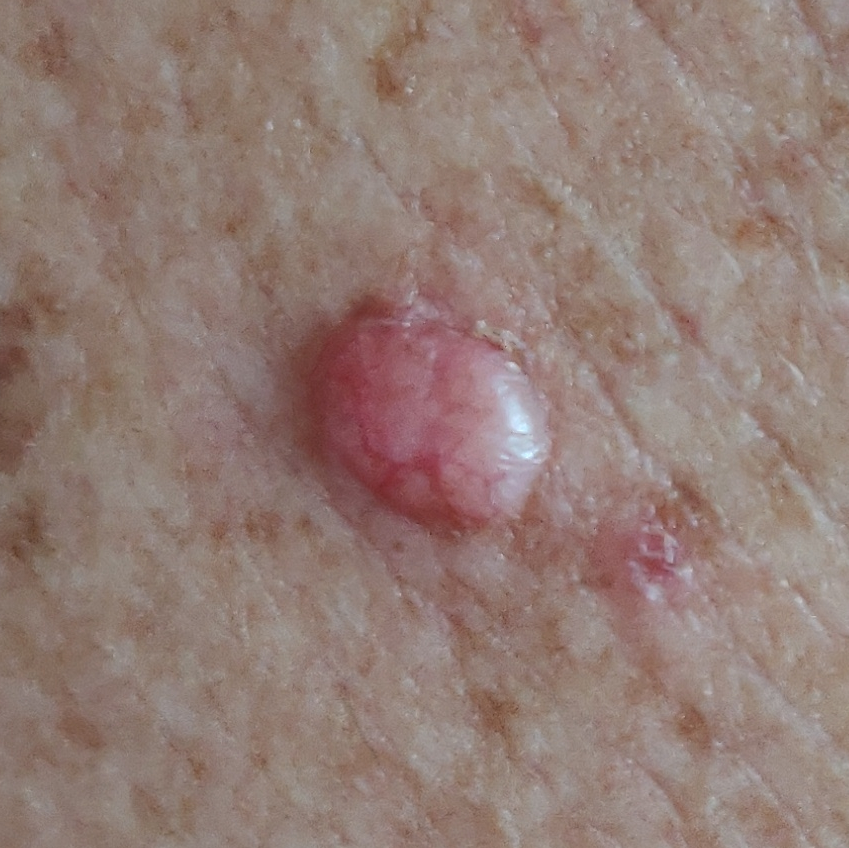The chart records prior malignancy (patient or family), pesticide exposure, and no prior skin cancer (patient or family). A smartphone photograph of a skin lesion. Fitzpatrick II. The lesion was found on the back. The lesion measures approximately 9 × 6 mm. By the patient's account, the lesion has changed, is elevated, itches, and has grown. The biopsy diagnosis was a basal cell carcinoma.